A skin lesion imaged with a dermatoscope.
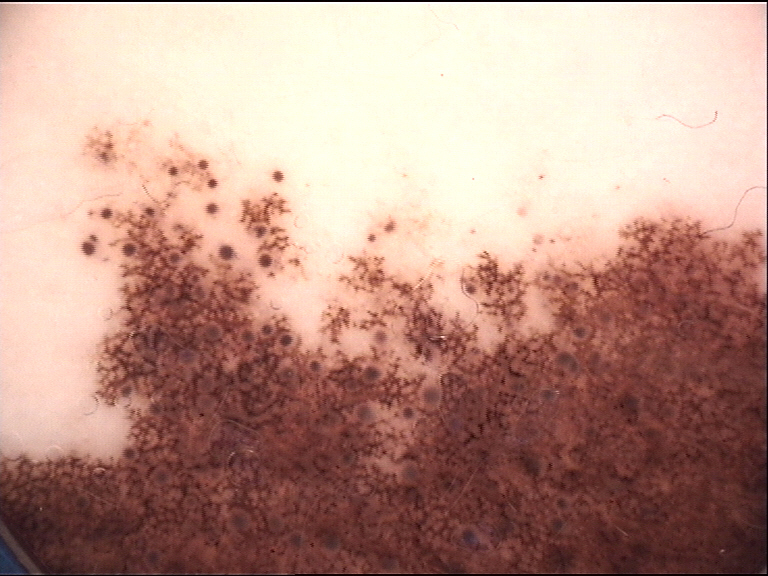Summary: This is a banal lesion. Impression: Consistent with a congenital compound nevus.